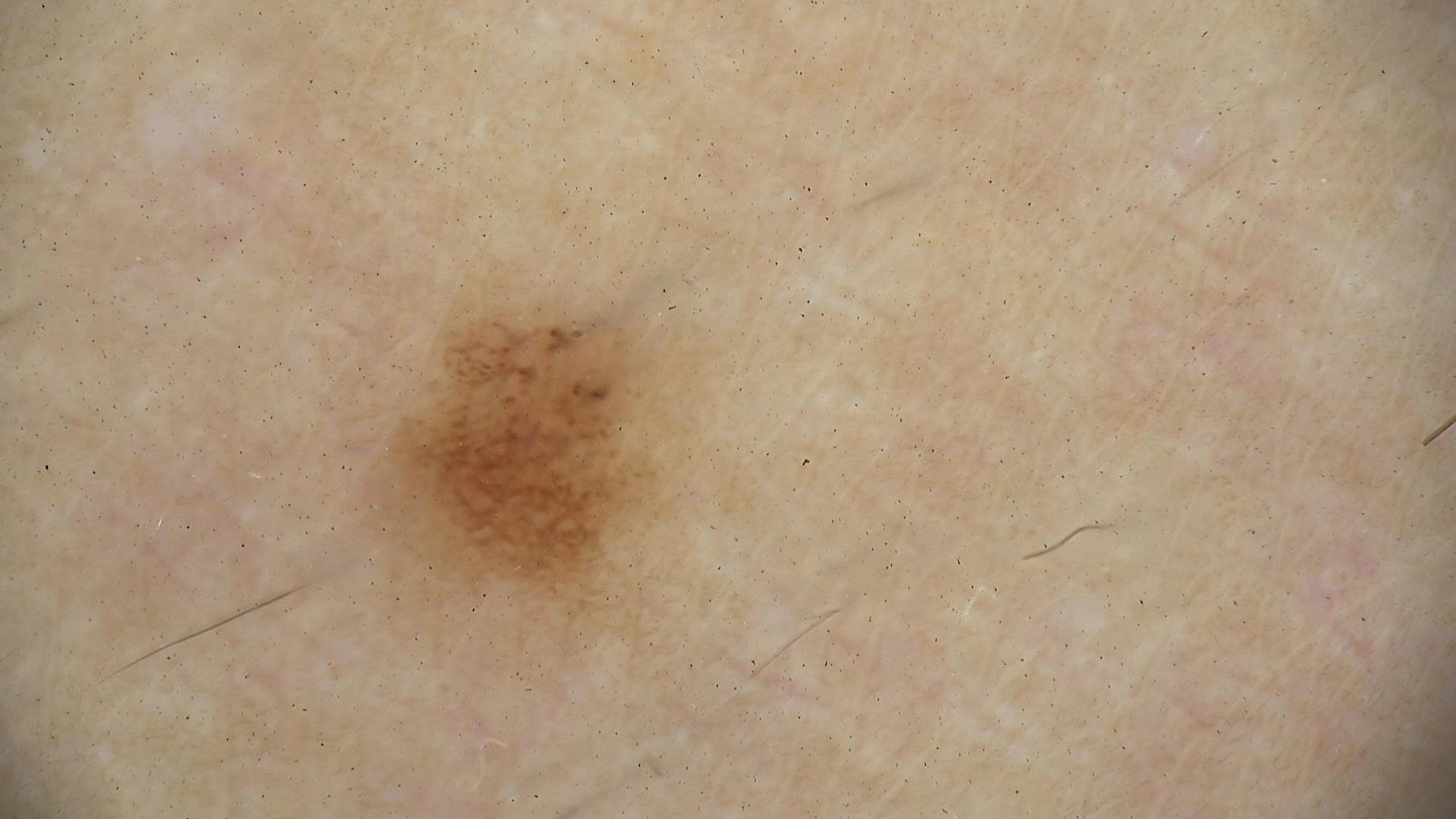A dermoscopic photograph of a skin lesion.
The diagnosis was a dysplastic junctional nevus.